Self-categorized by the patient as a rash; the patient reported no systemic symptoms; a close-up photograph; the lesion is associated with darkening, bothersome appearance, burning, pain, bleeding and itching; the patient notes the condition has been present for less than one week; located on the leg — 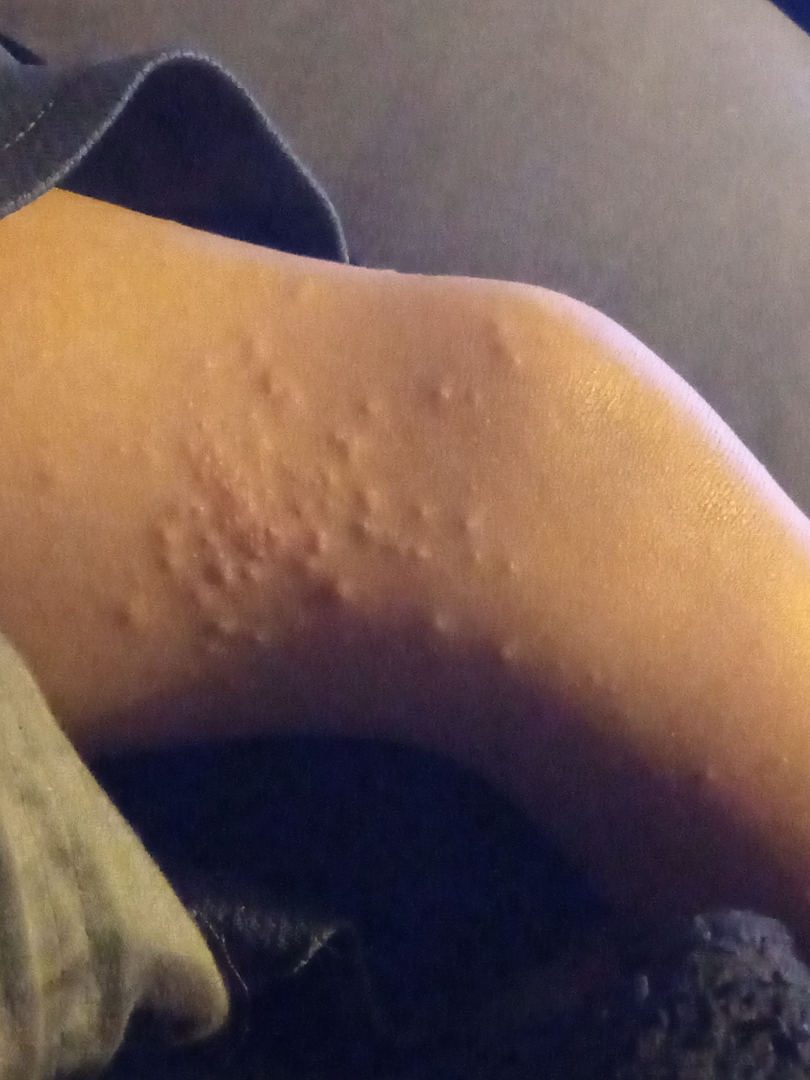assessment=indeterminate